The patient is a female aged 30–39. The affected area is the arm and leg. The photograph is a close-up of the affected area. The lesion is described as raised or bumpy. The patient considered this a rash:
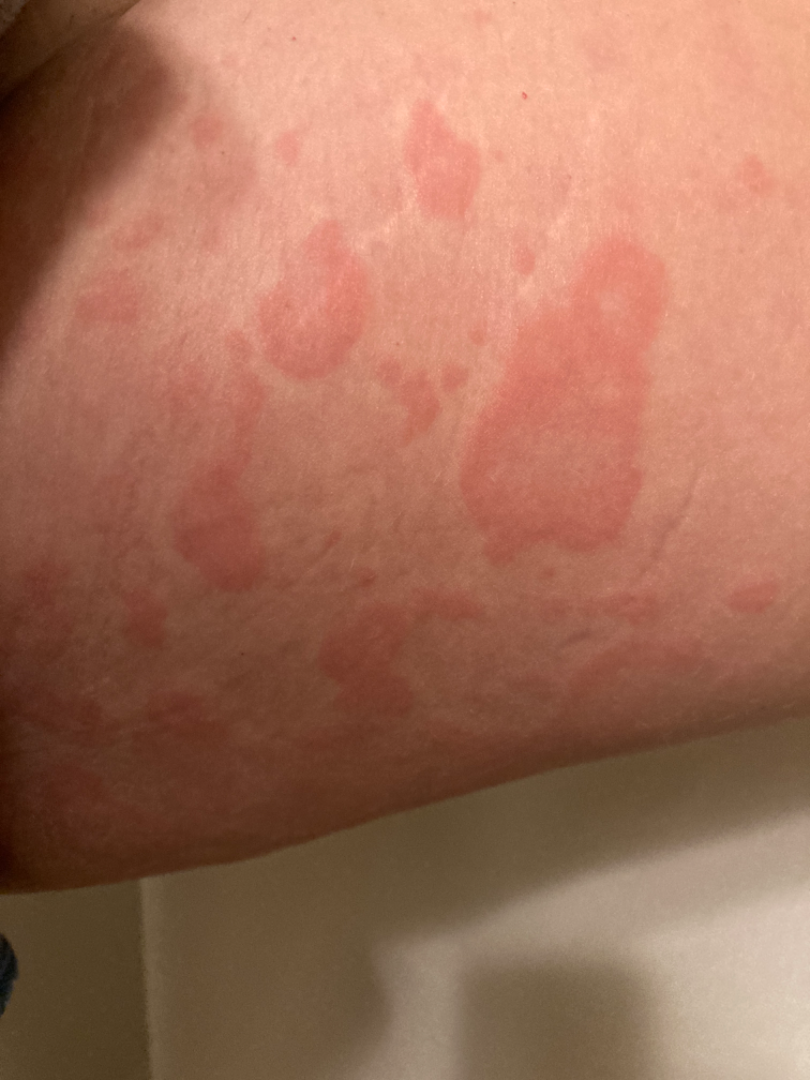On remote dermatologist review: Drug Rash (possible); Urticaria (possible); Leukocytoclastic Vasculitis (possible).